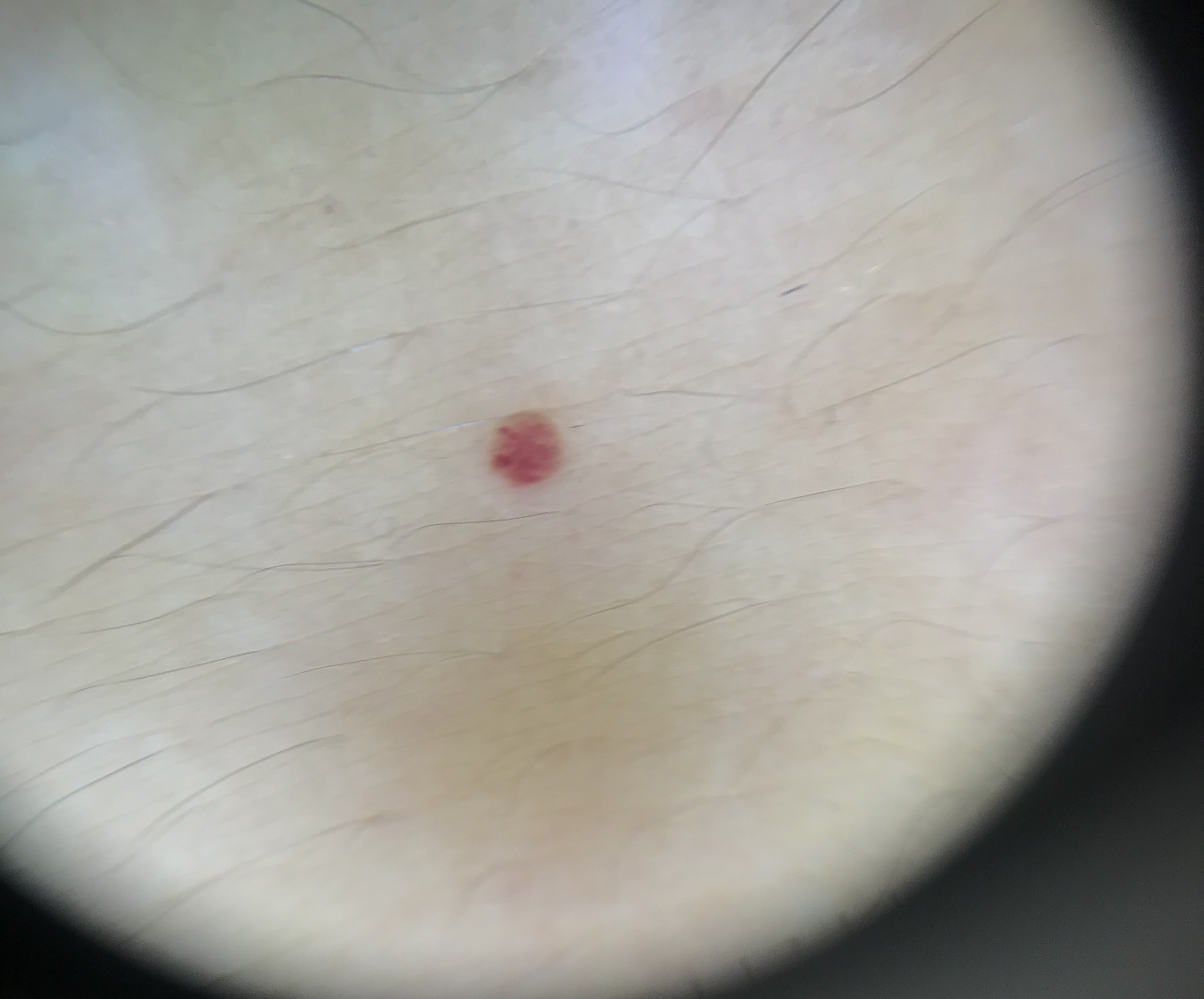image type = dermatoscopy | class = hemangioma (expert consensus).